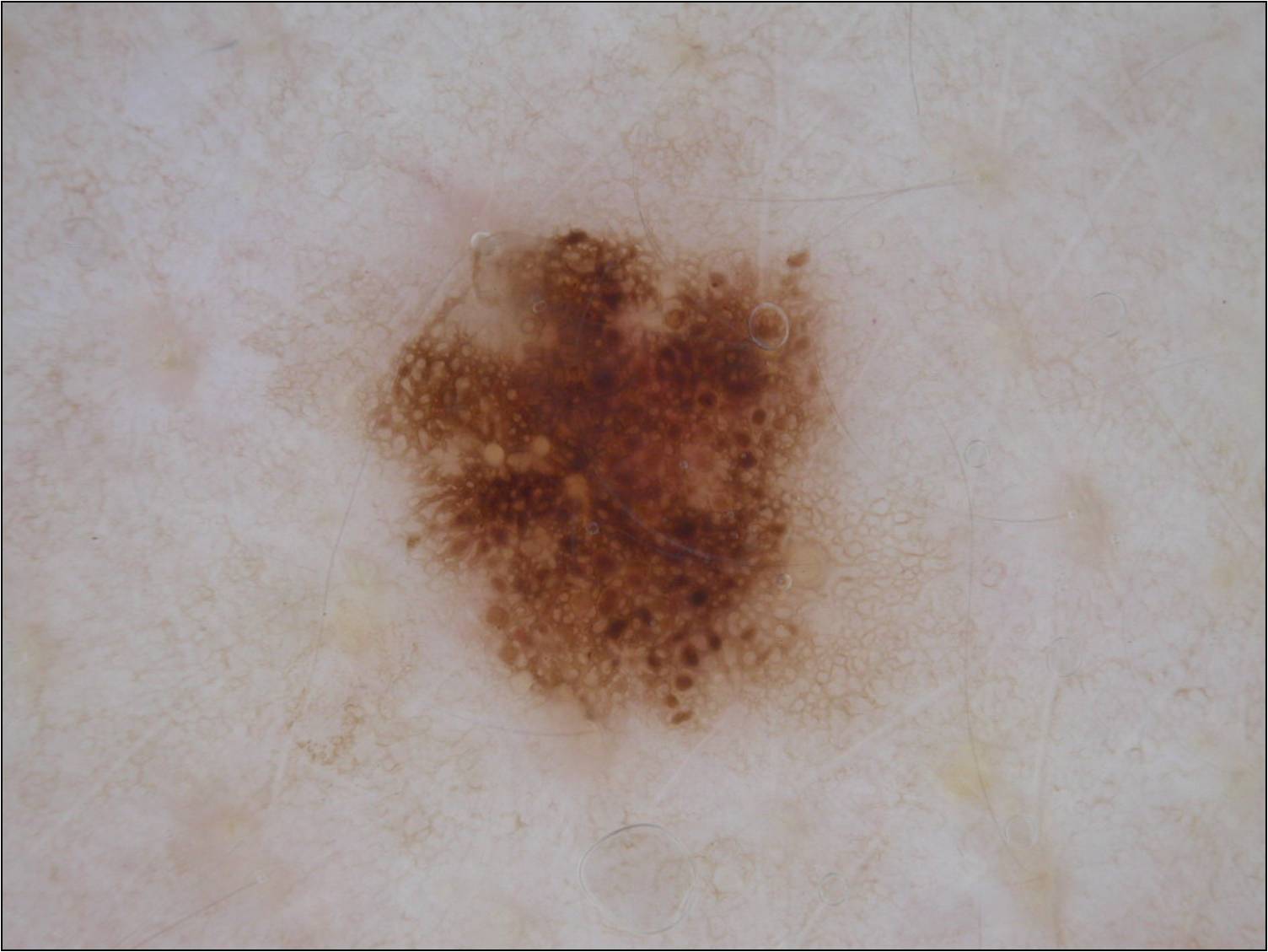| feature | finding |
|---|---|
| image | dermoscopic image |
| extent | moderate |
| features | pigment network and globules; absent: milia-like cysts, negative network, and streaks |
| lesion bbox | [360, 223, 835, 732] |
| impression | a melanocytic nevus |